The patient is a female aged approximately 45 · a dermoscopic view of a skin lesion: 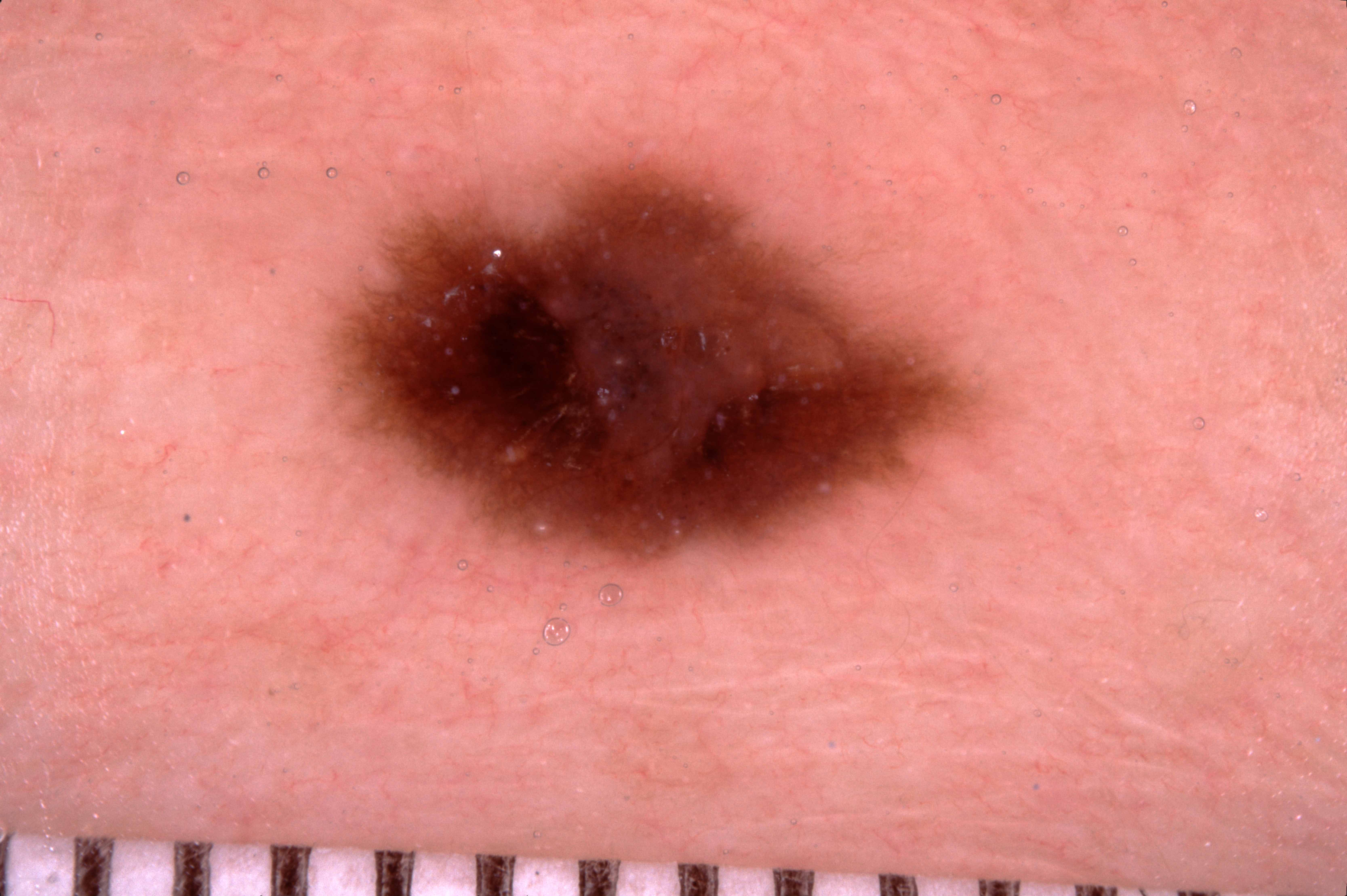Summary: The lesion takes up about 16% of the image. Dermoscopic review identifies pigment network and milia-like cysts. The lesion is located at (320, 154, 987, 575). Assessment: Expert review diagnosed this as a melanocytic nevus, a benign skin lesion.